Imaged for a research study, with no referral diagnosis recorded; the patient says their skin reddens with sun exposure; a female patient 73 years old; a dermatoscopic image of a skin lesion; the patient describes having few moles overall: 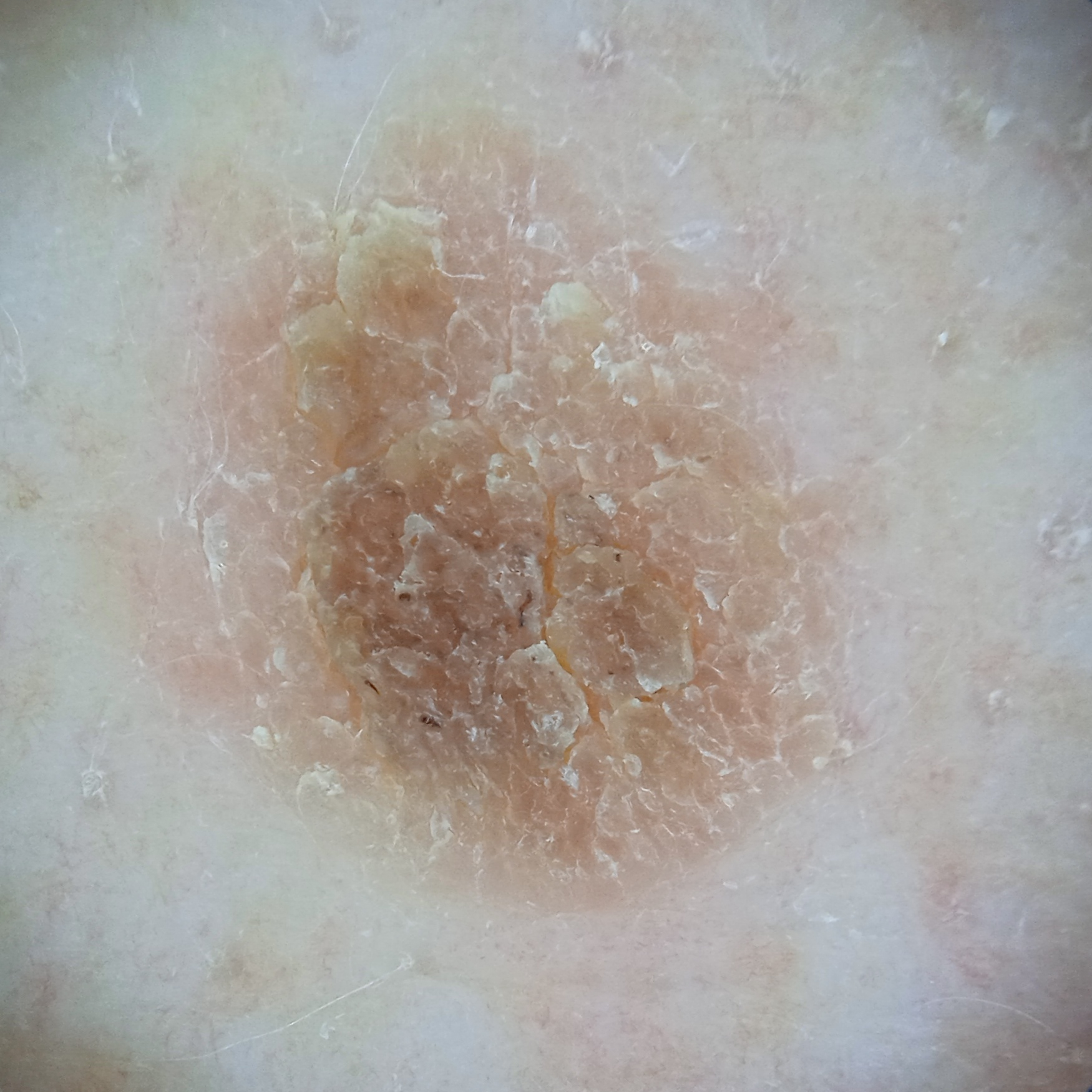| field | value |
|---|---|
| location | the back |
| size | 8.6 mm |
| diagnostic label | seborrheic keratosis (dermatologist consensus) |